A skin lesion imaged with a dermatoscope: 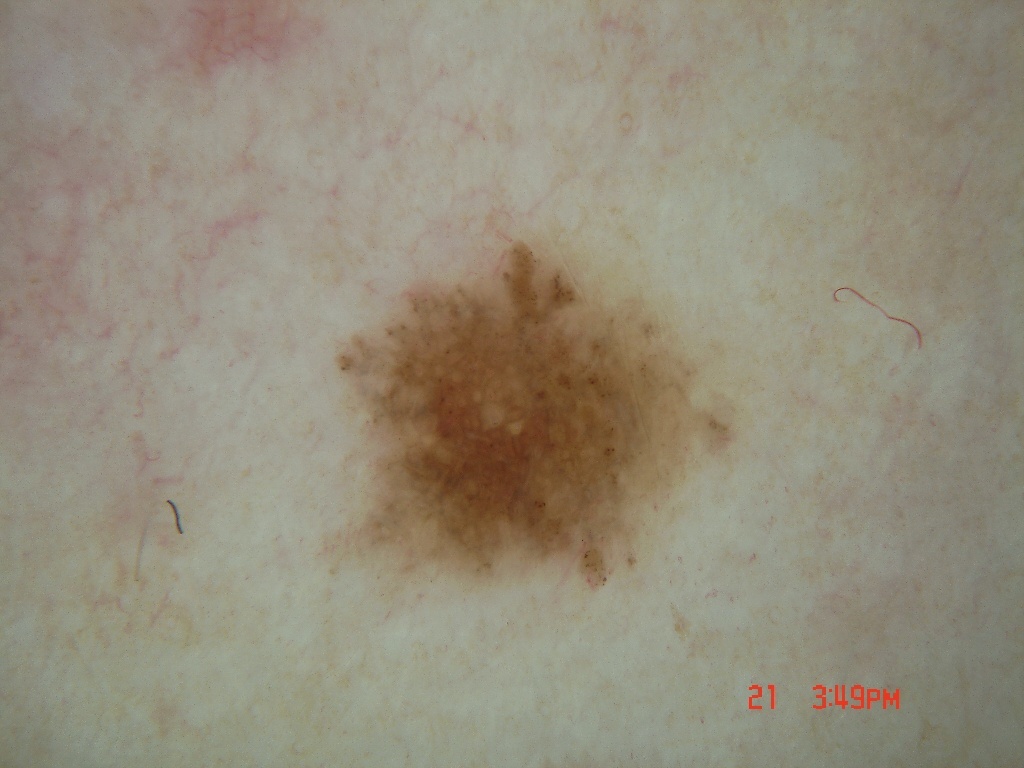Dermoscopically, the lesion shows pigment network; no negative network, streaks, globules, or milia-like cysts. In (x1, y1, x2, y2) order, the lesion spans 328/229/739/591. The lesion takes up about 13% of the image. Histopathologically confirmed as a melanoma, a skin cancer.